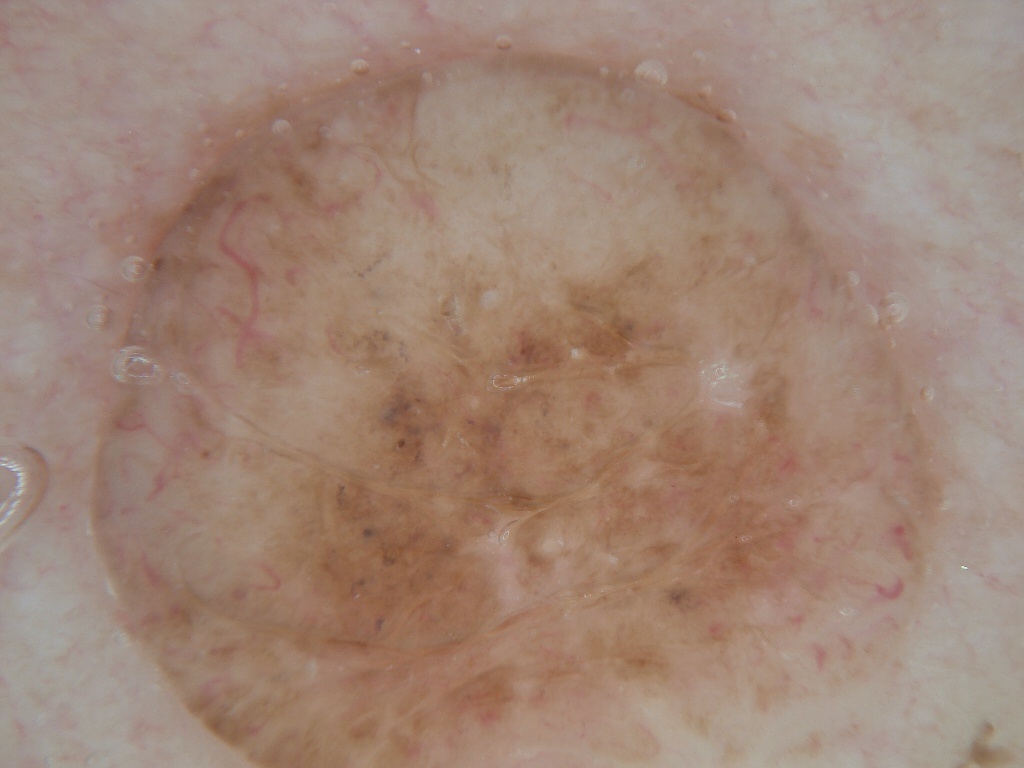imaging — dermoscopy
bounding box — x1=80 y1=36 x2=954 y2=766
impression — a melanocytic nevus